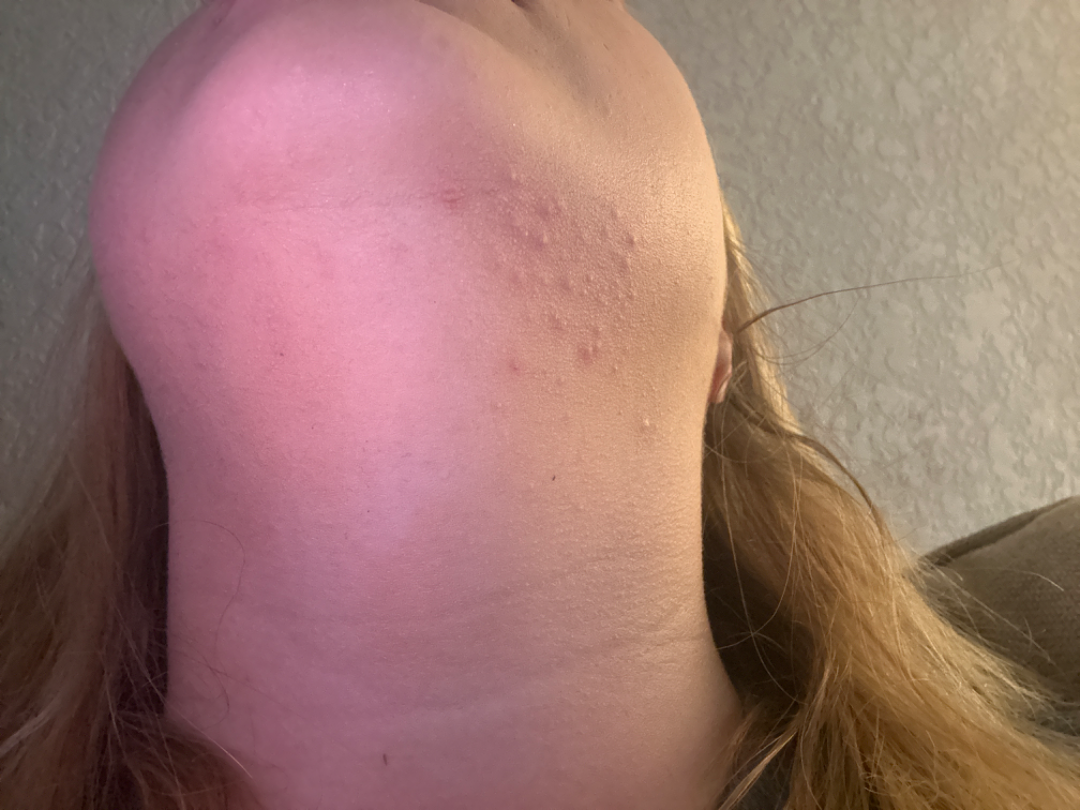Review:
On photographic review: the reviewer's impression was Acne.